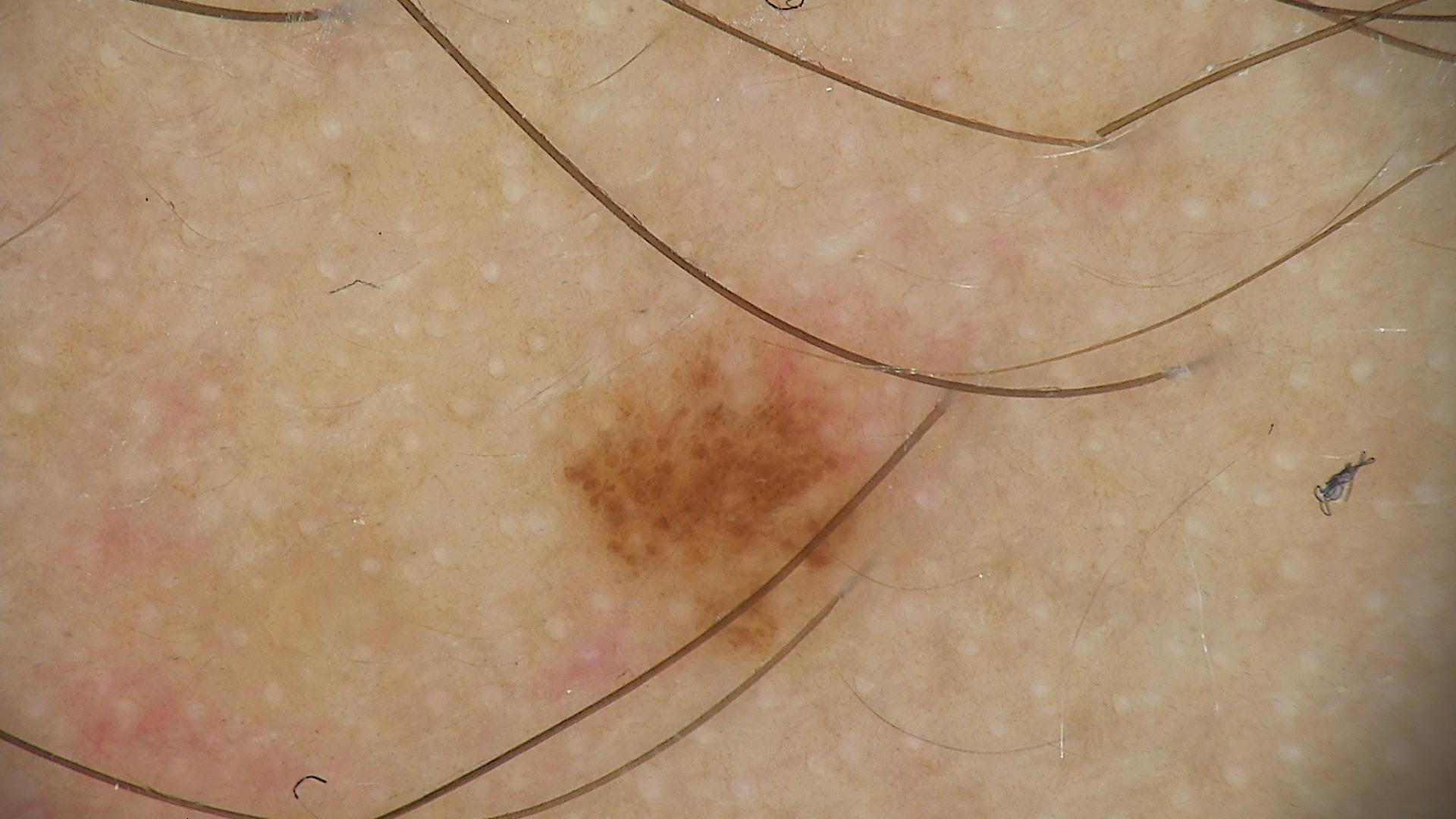Consistent with a benign lesion — a dysplastic junctional nevus.